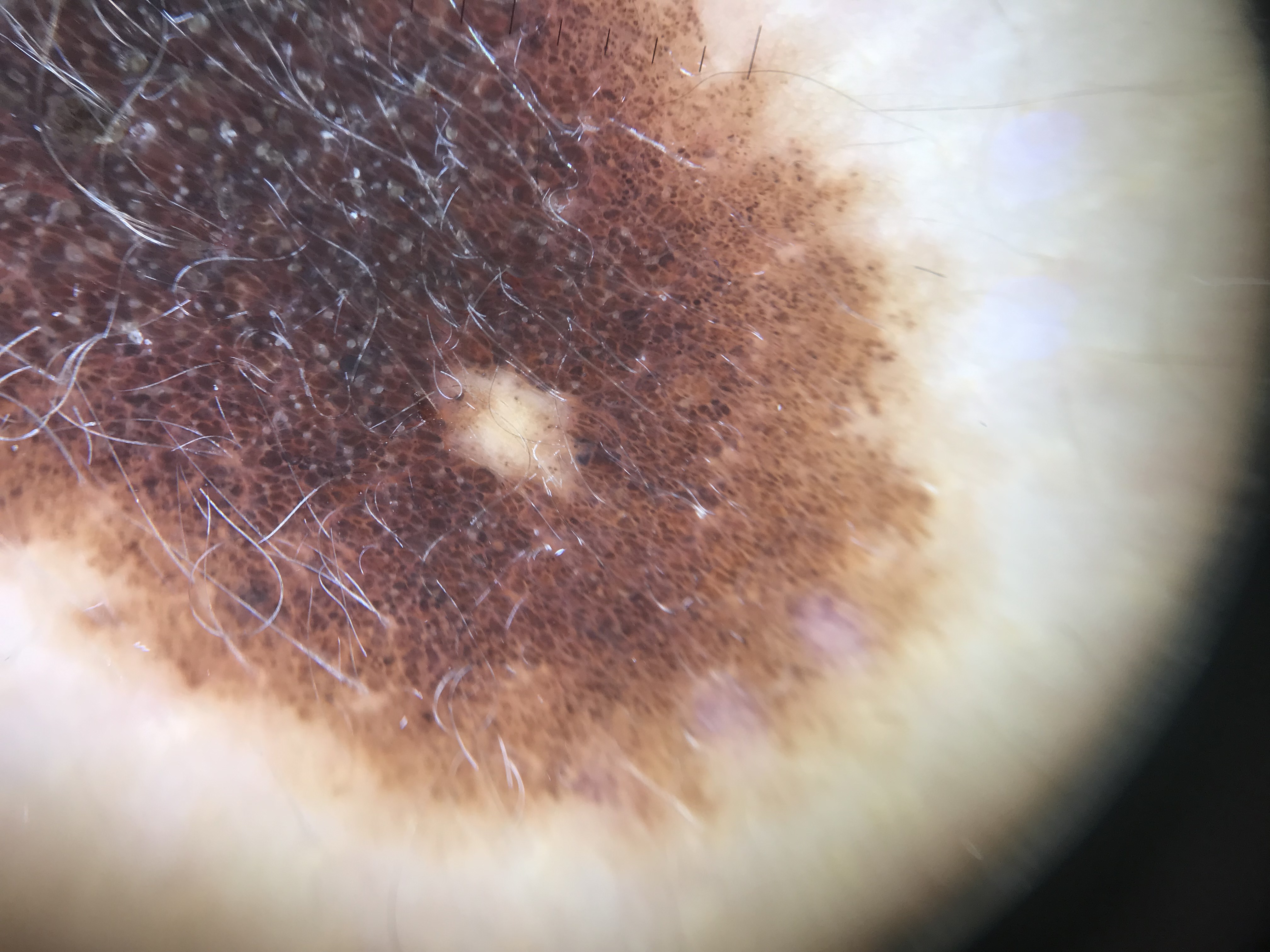The morphology is that of a banal lesion. The diagnosis was a congenital compound nevus.